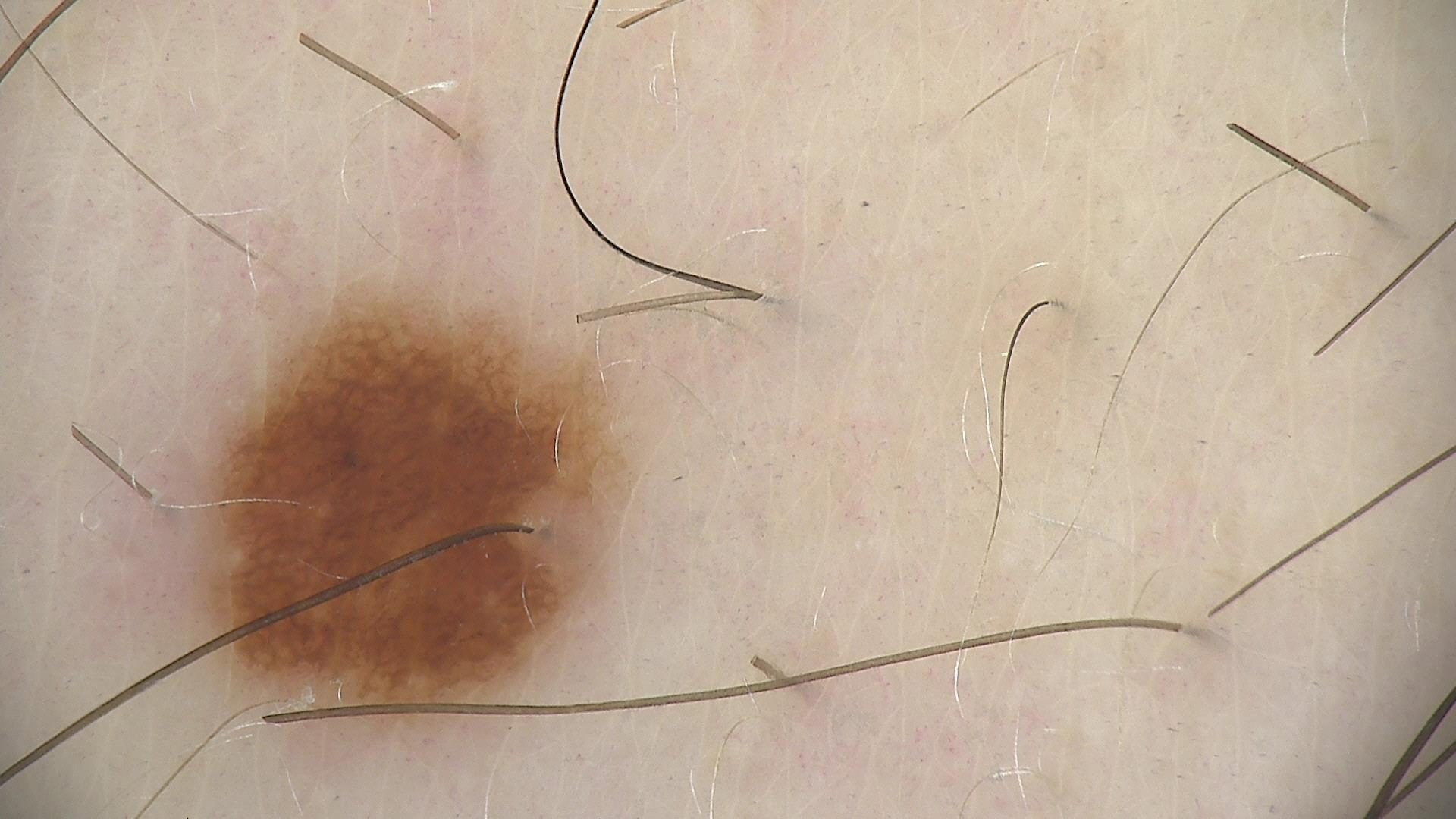A dermoscopic photograph of a skin lesion.
Classified as a dysplastic junctional nevus.